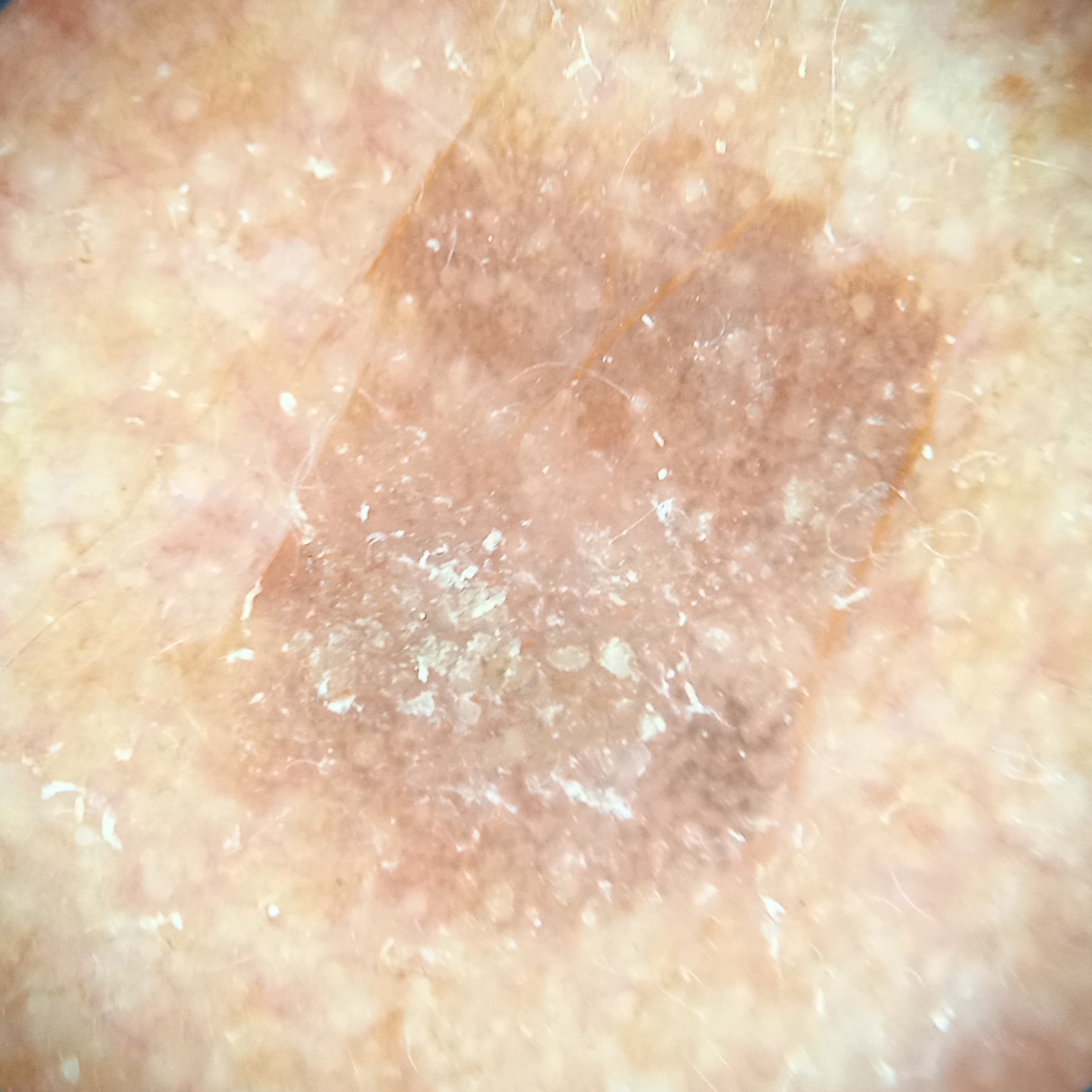patient = male, 76 years old; referral = clinical suspicion of basal cell carcinoma; imaging = dermoscopy; risk factors = a personal history of cancer, a personal history of skin cancer; sun reaction = skin reddens with sun exposure; nevus count = few melanocytic nevi overall; anatomic site = the face; diameter = 8.7 mm; pathology = basal cell carcinoma (biopsy-proven).